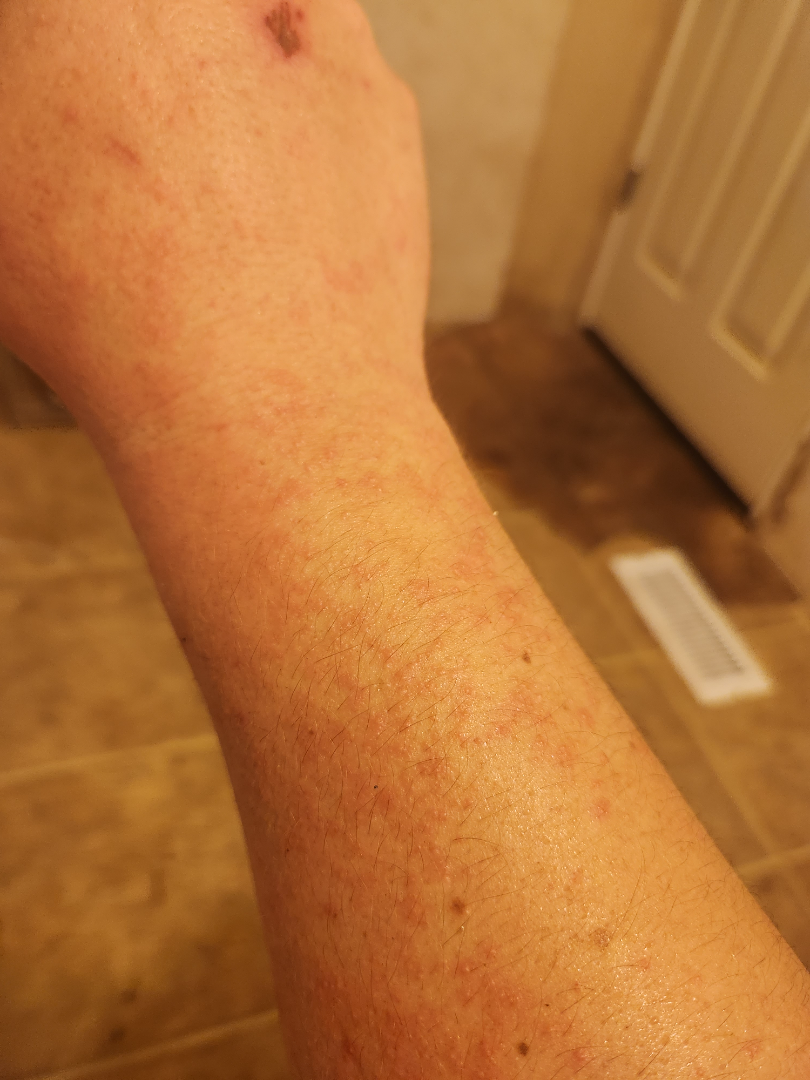  body_site: arm
  symptoms: itching
  shot_type: close-up
  texture: raised or bumpy
  differential:
    leading:
      - Allergic Contact Dermatitis
    considered:
      - Drug Rash
      - Viral Exanthem